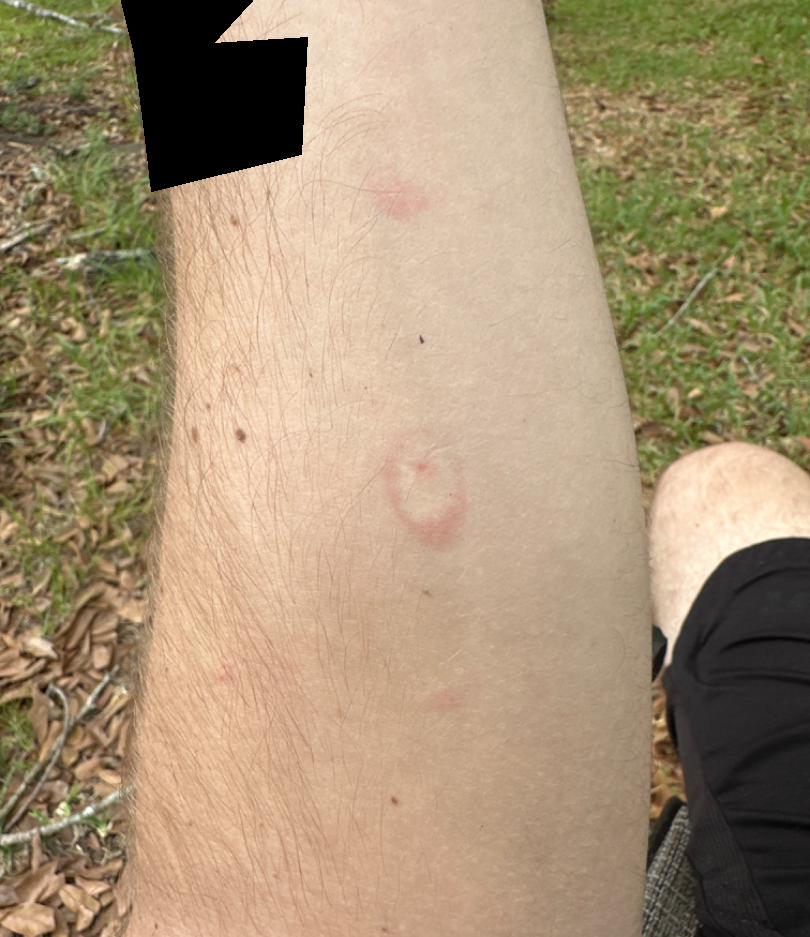The reviewing dermatologist was unable to assign a differential diagnosis from the image. A close-up photograph. Located on the arm.